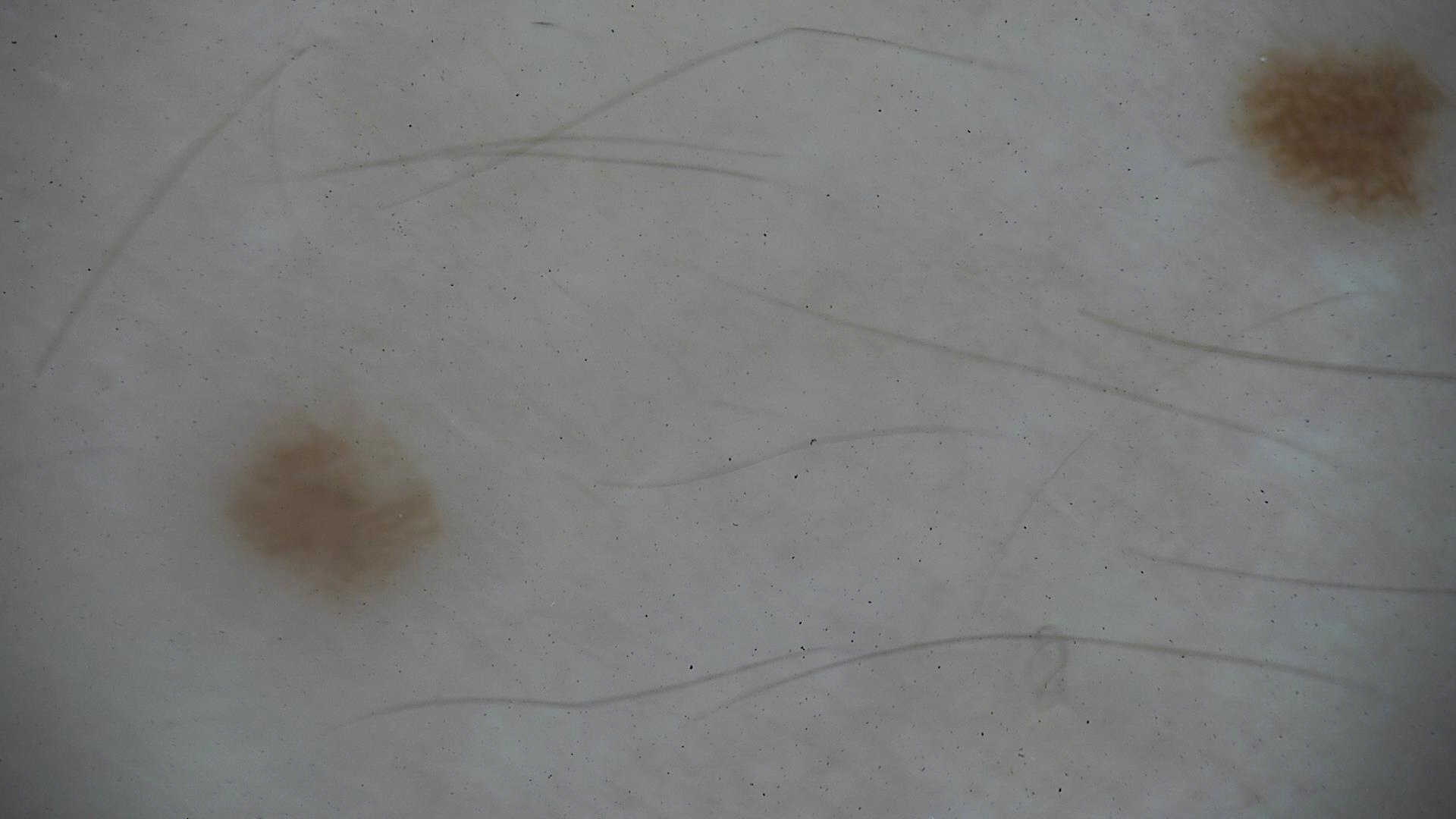Findings:
A dermoscopic photograph of a skin lesion.
Conclusion:
The diagnosis was a benign lesion — a dysplastic junctional nevus.